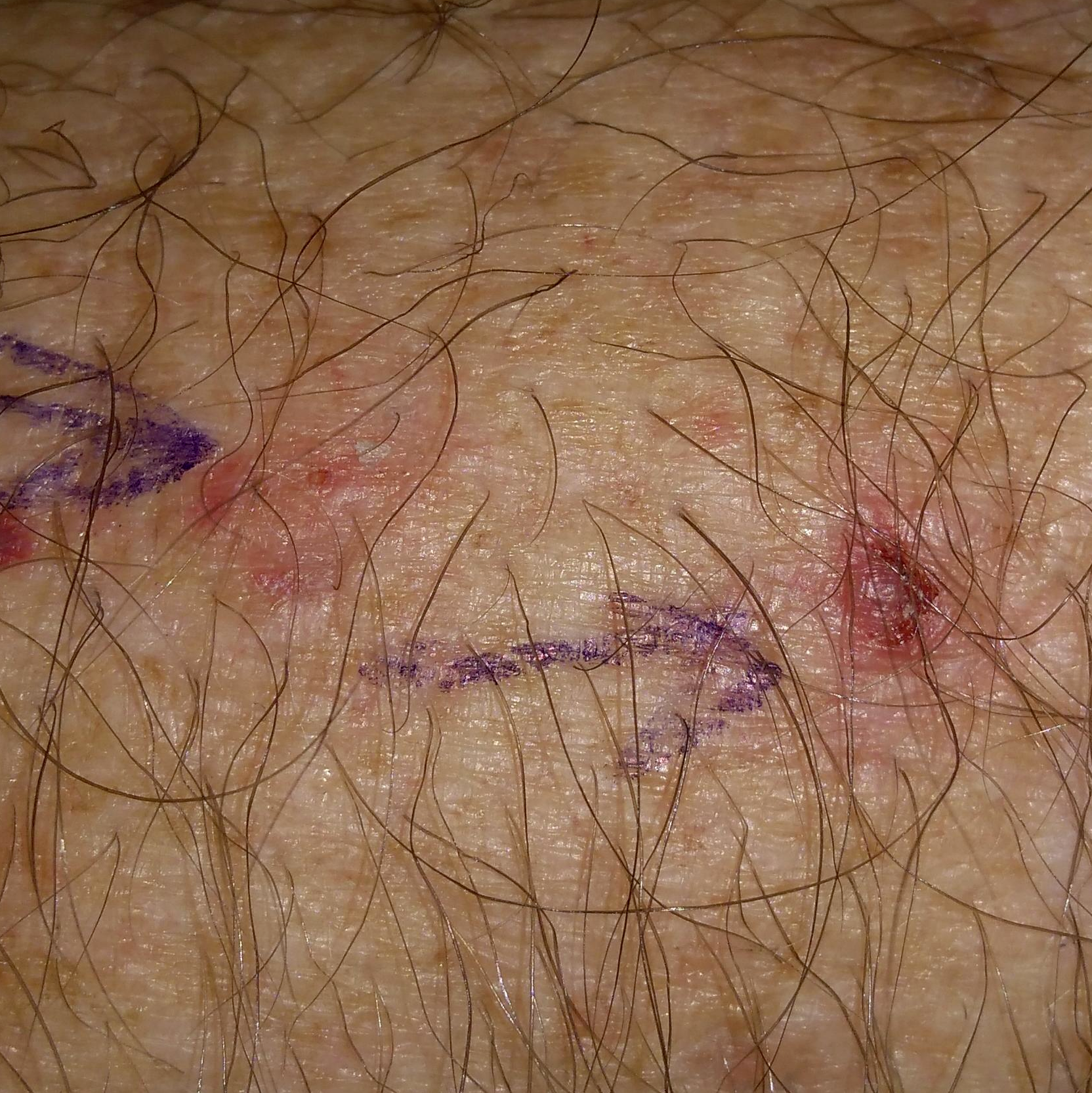Q: How was this image acquired?
A: clinical photo
Q: Patient demographics?
A: 36 years of age
Q: What is the anatomic site?
A: a forearm
Q: Any reported symptoms?
A: growth, bleeding, itching
Q: What is this lesion?
A: actinic keratosis (clinical consensus)